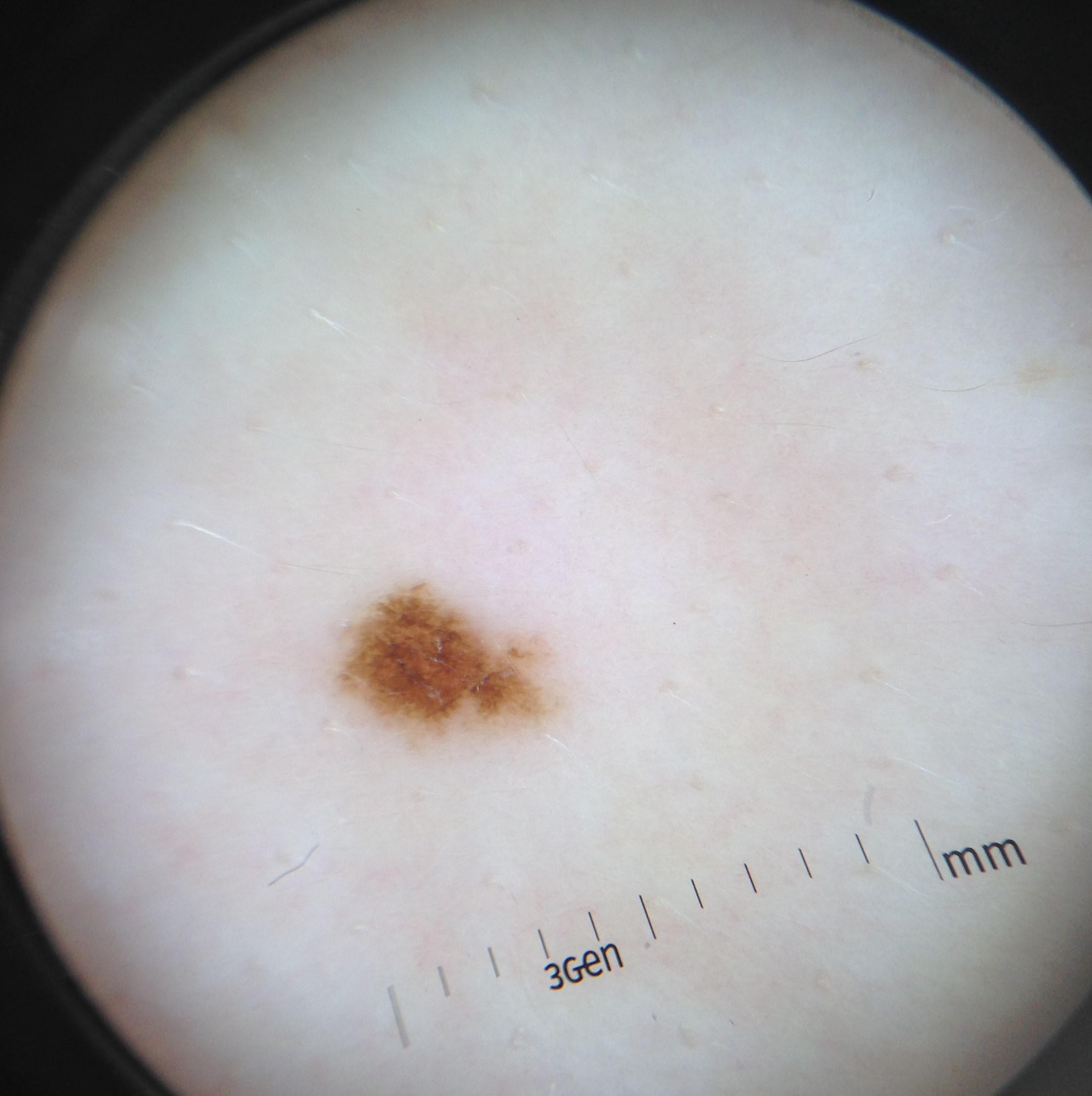diagnosis: dysplastic junctional nevus (expert consensus).